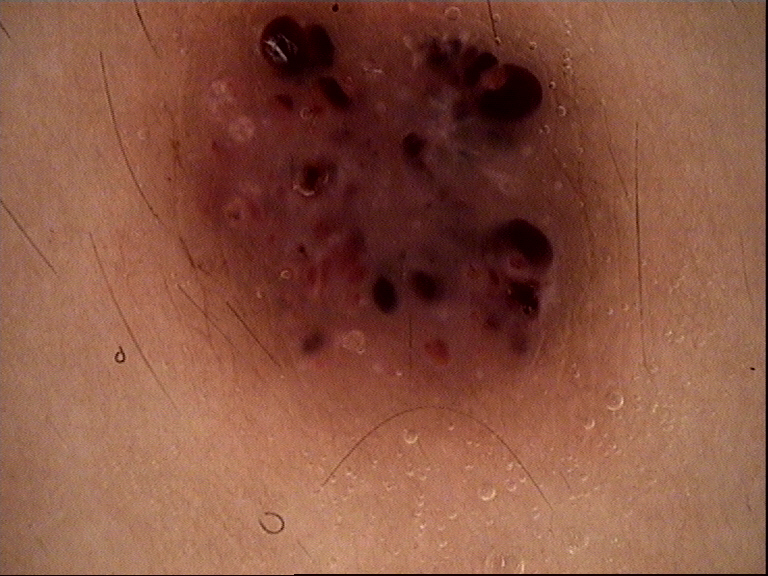imaging: dermatoscopy | category: vascular | assessment: angiokeratoma (expert consensus).